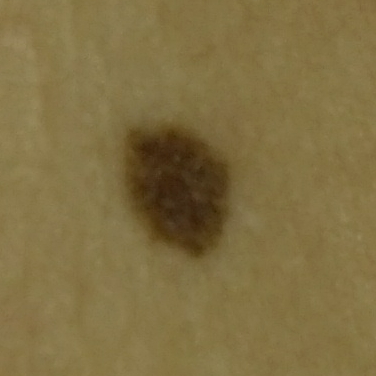A clinical photo of a skin lesion taken with a smartphone. The patient is Fitzpatrick skin type II. A female patient 52 years of age. History notes no tobacco use and no alcohol use. The lesion is roughly 4 by 2 mm. By the patient's account, the lesion does not hurt and has not bled. Histopathology confirmed a nevus.